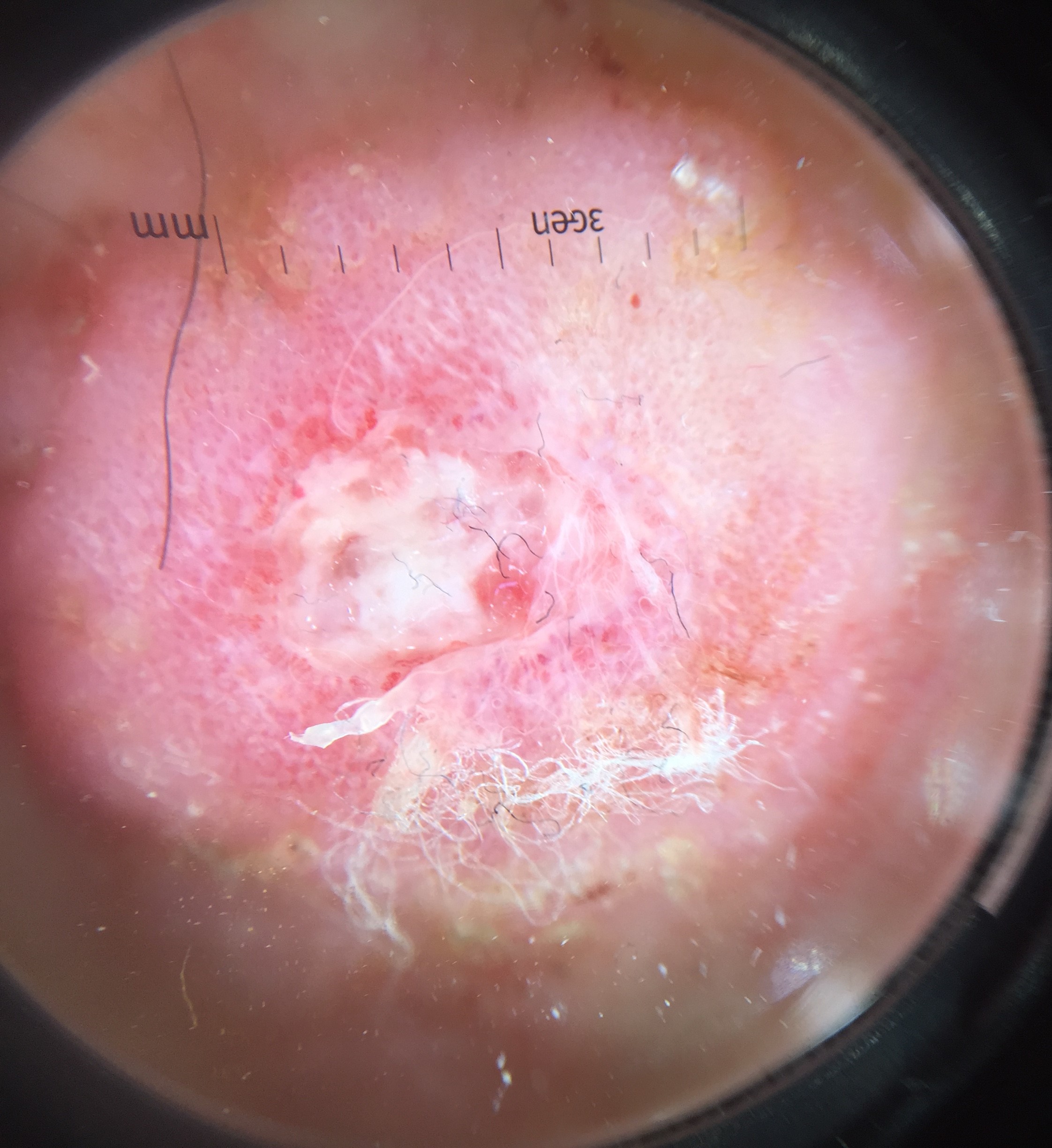Confirmed on histopathology as a squamous cell carcinoma.